A skin lesion imaged with a dermatoscope — 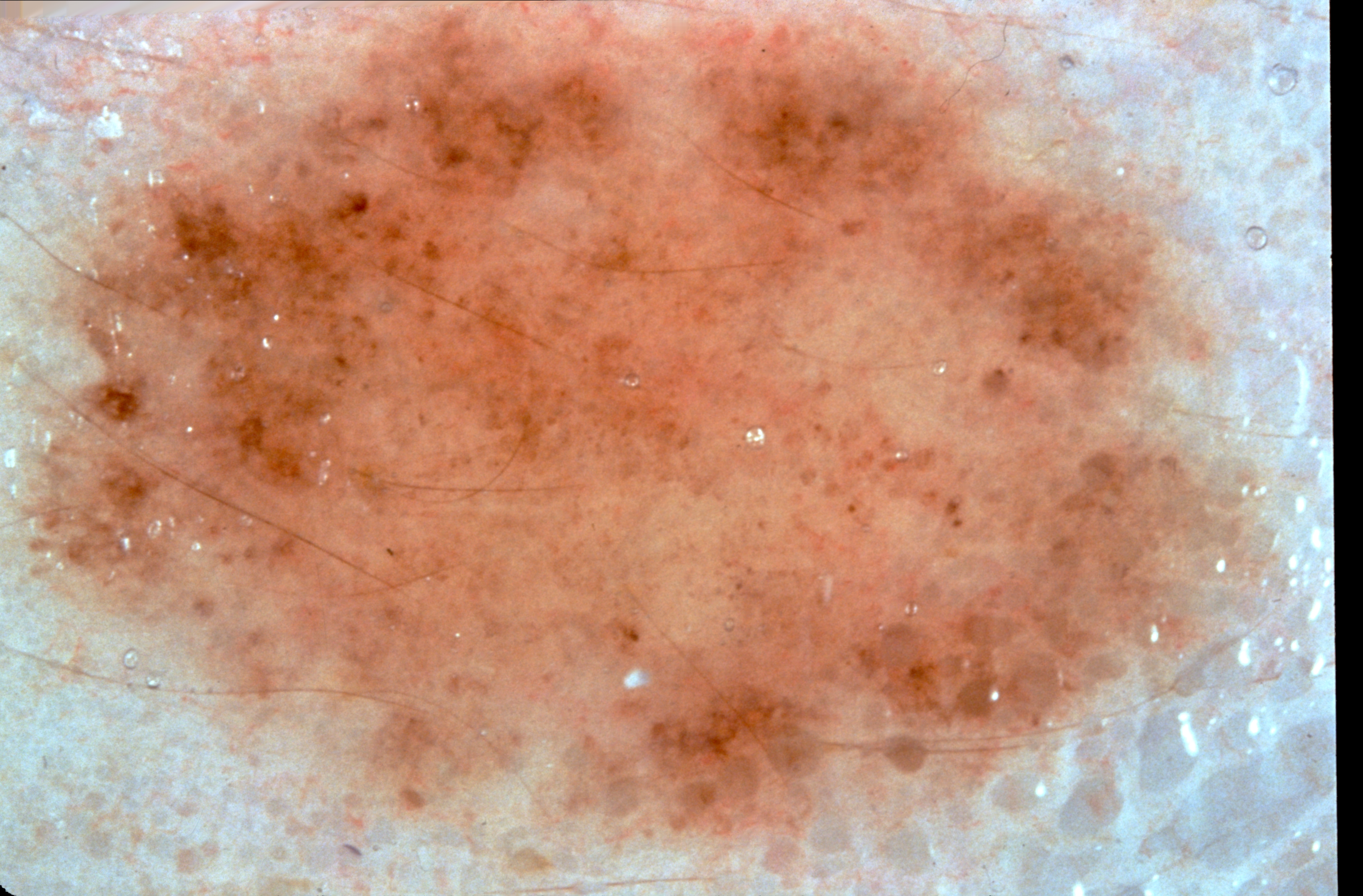The dermoscopic pattern shows no streaks, milia-like cysts, pigment network, or negative network. The lesion reaches across nearly the entire image. The diagnostic assessment was a melanocytic nevus, a benign skin lesion.